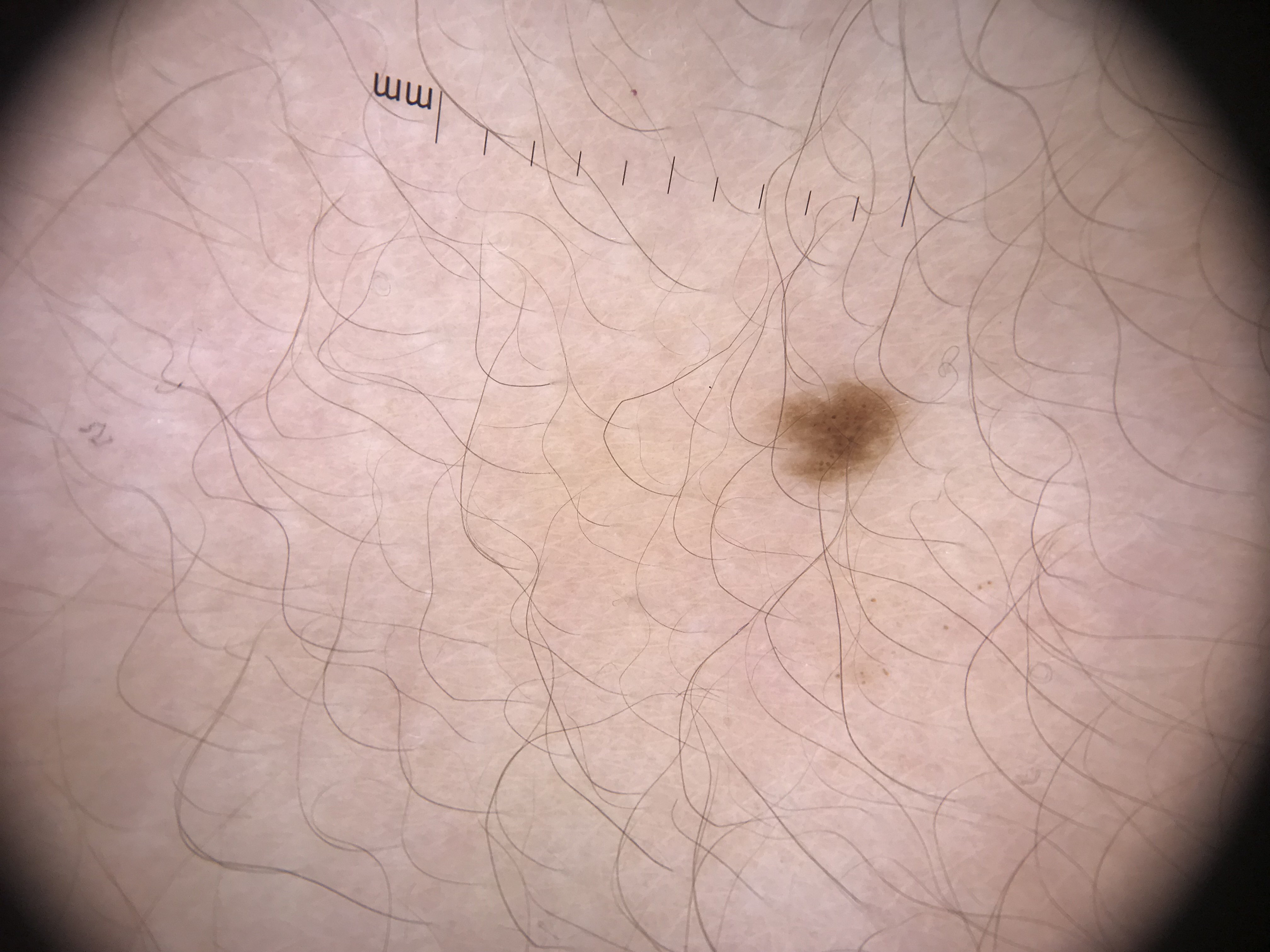diagnostic label=junctional nevus (expert consensus).